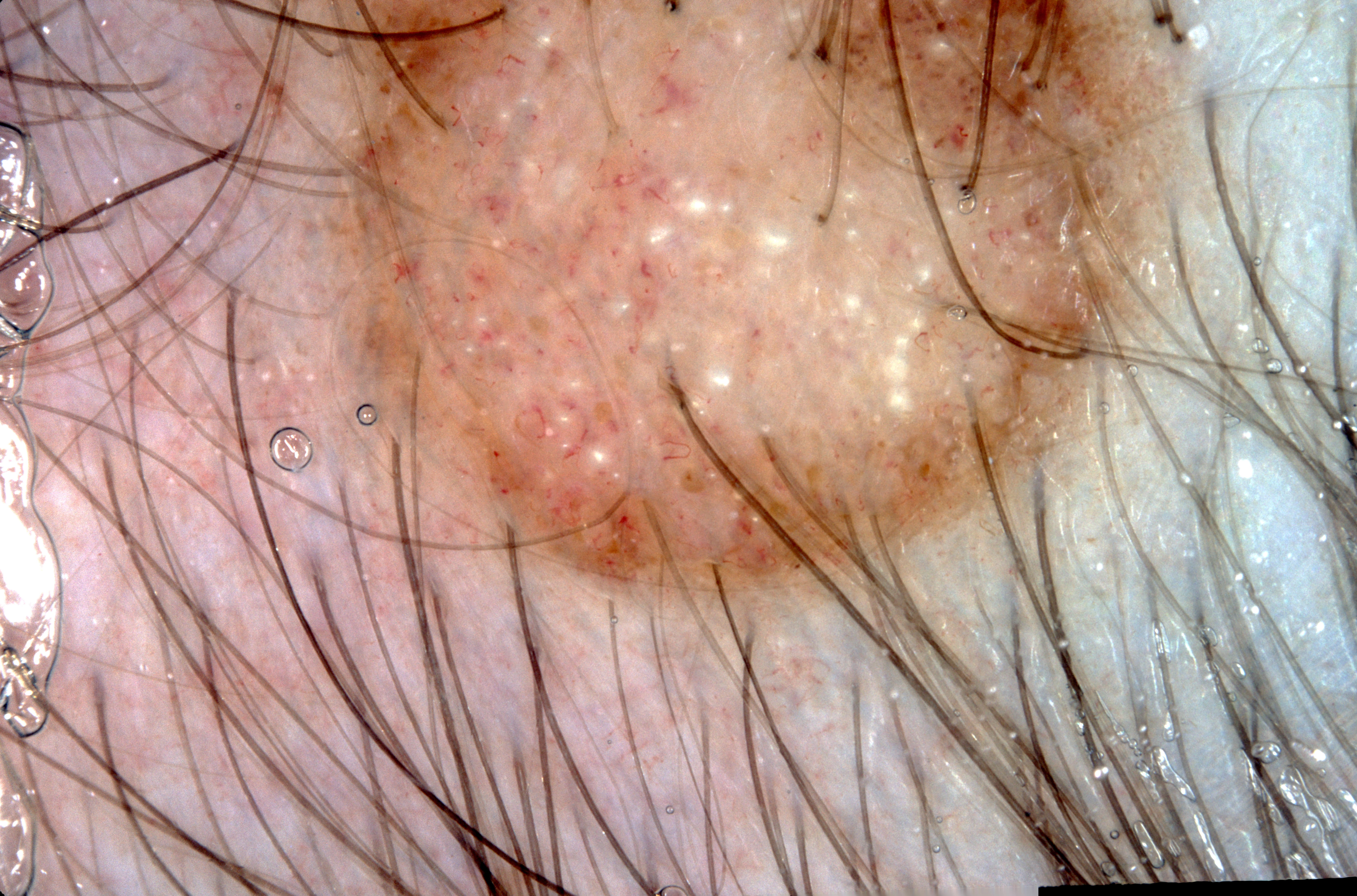Case summary: A female subject about 20 years old. This is a dermoscopic photograph of a skin lesion. Dermoscopic assessment notes milia-like cysts. With coordinates (x1, y1, x2, y2), the lesion is located at bbox=[280, 1, 1231, 626]. Impression: The lesion was assessed as a melanocytic nevus, a benign skin lesion.